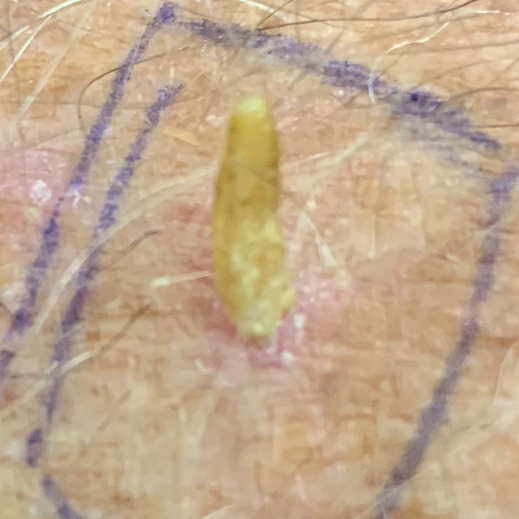patient: male, 71 years old; imaging: clinical photo; FST: II; site: a forearm; size: 5 × 4 mm; patient-reported symptoms: elevation, pain, growth; diagnostic label: actinic keratosis (biopsy-proven).